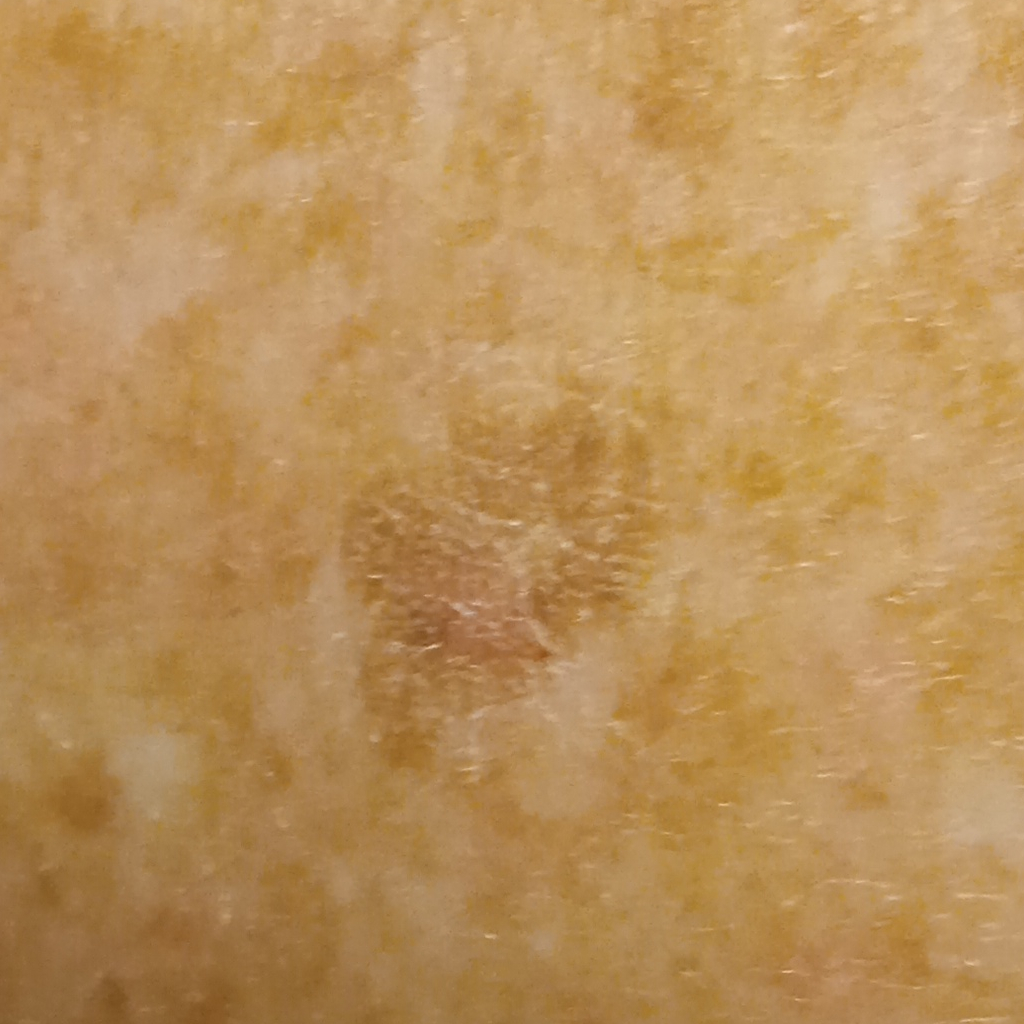The patient says their skin reddens with sun exposure. The patient reports a personal history of cancer. Numerous moles by the patient's own estimate. Collected as part of a research study, without a referral diagnosis. The lesion involves the back. The lesion measures approximately 10.7 mm. The dermatologists' assessment was a seborrheic keratosis.